A dermoscopy image of a single skin lesion; a male subject aged approximately 60: 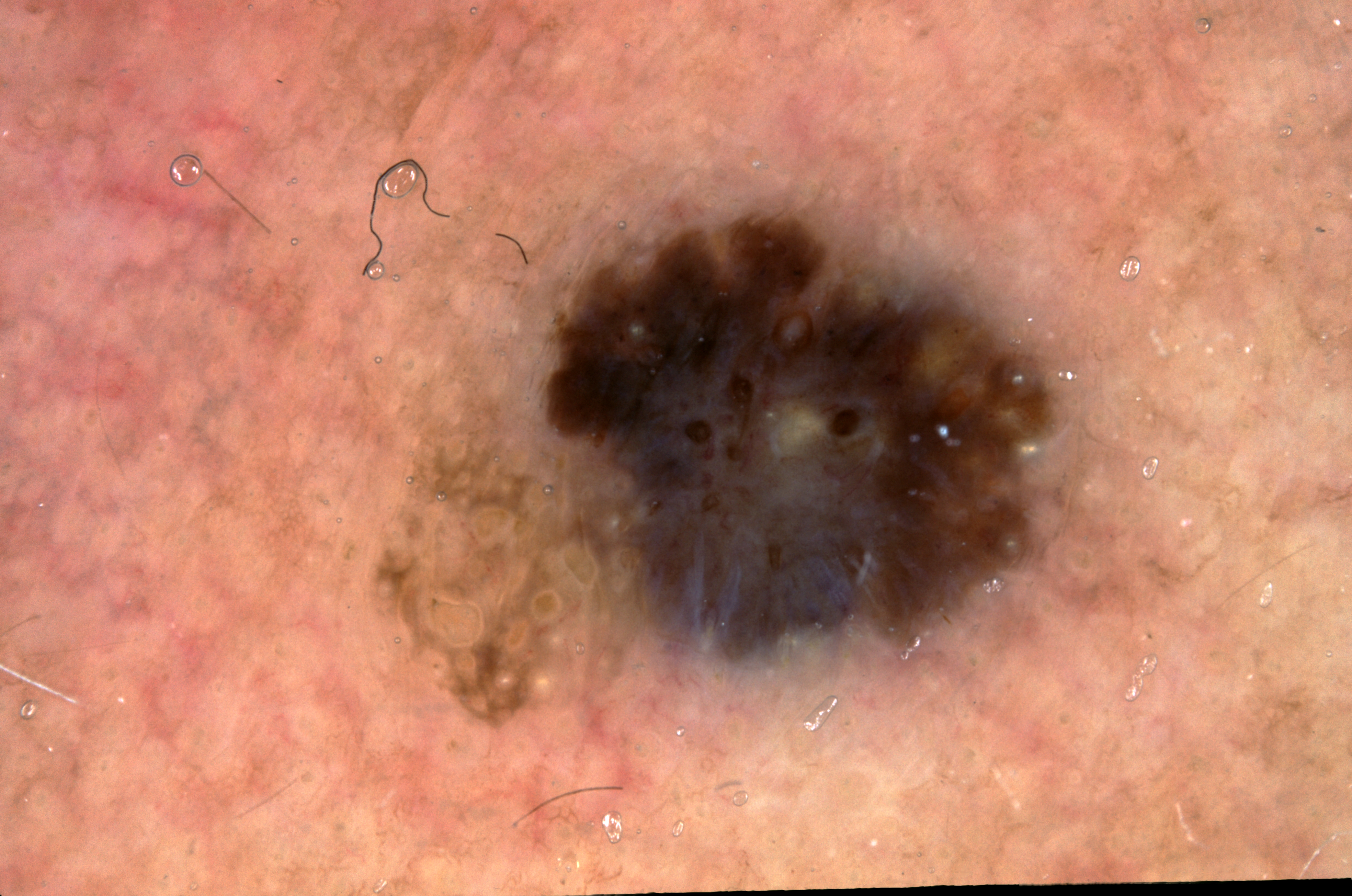Dermoscopic assessment notes milia-like cysts.
As (left, top, right, bottom), the lesion is located at <bbox>358, 165, 1097, 731</bbox>.
A moderately sized lesion.
The clinical diagnosis was a seborrheic keratosis, a benign skin lesion.